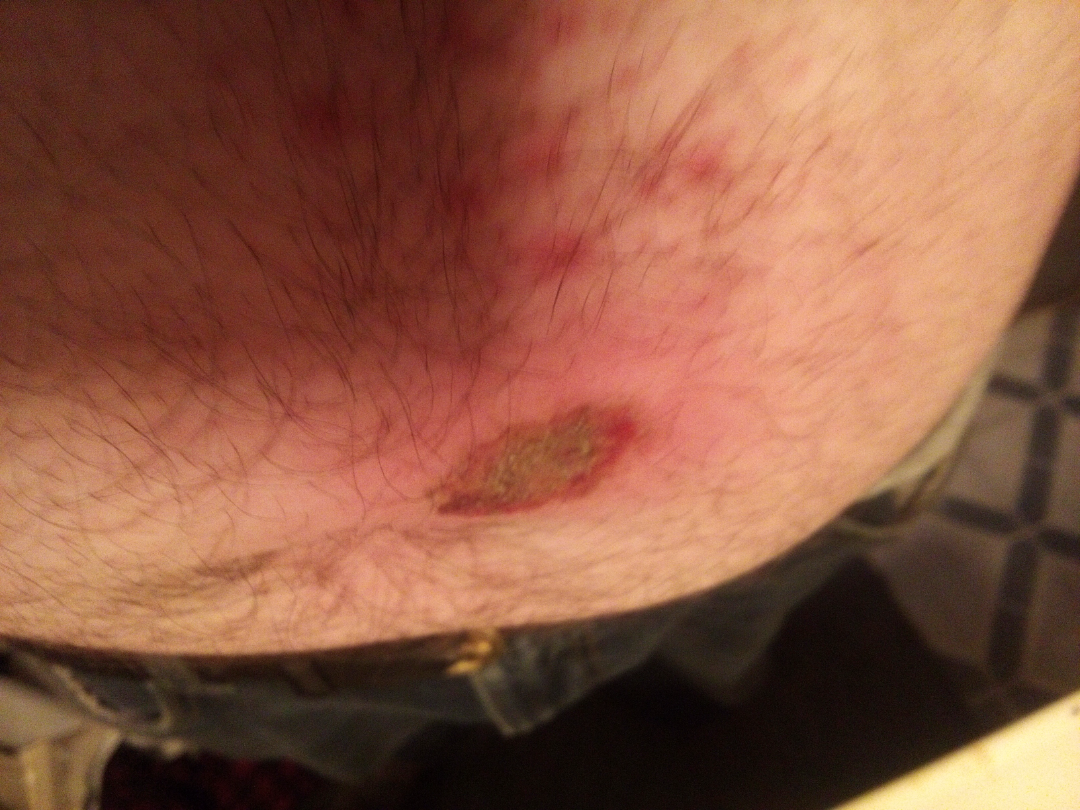The reviewing dermatologist was unable to assign a differential diagnosis from the image.